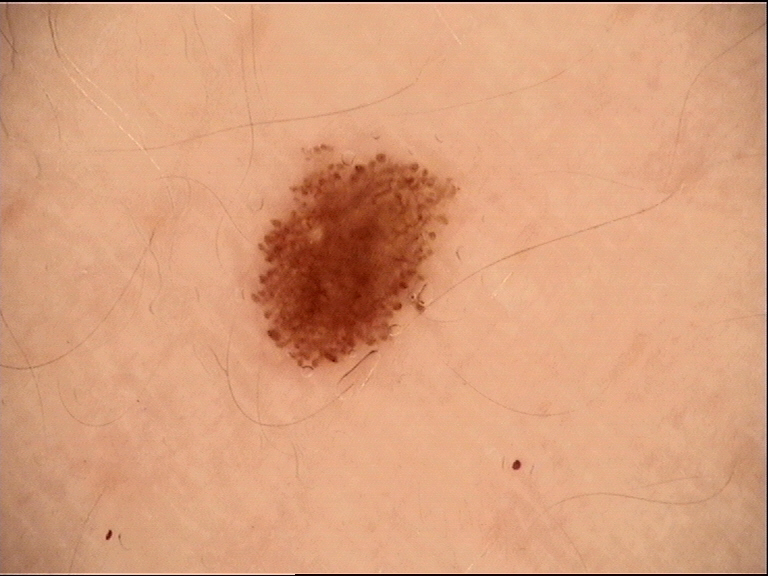A dermoscopy image of a single skin lesion. The diagnostic label was a benign lesion — a dysplastic junctional nevus.